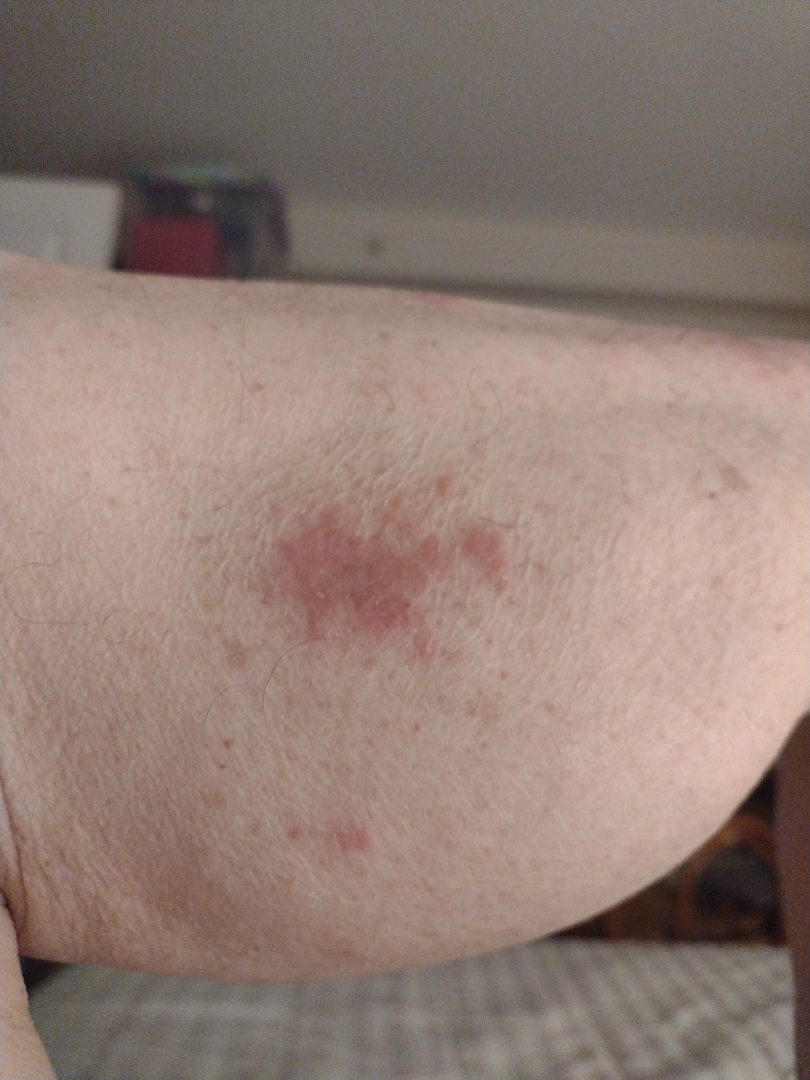The dermatologist could not determine a likely condition from the photograph alone.
This is a close-up image.
The patient considered this a rash.
No constitutional symptoms were reported.
Reported duration is one to three months.
Male subject, age 70–79.
The lesion is described as raised or bumpy.
Symptoms reported: itching.
The lesion involves the leg.